A dermoscopic photograph of a skin lesion.
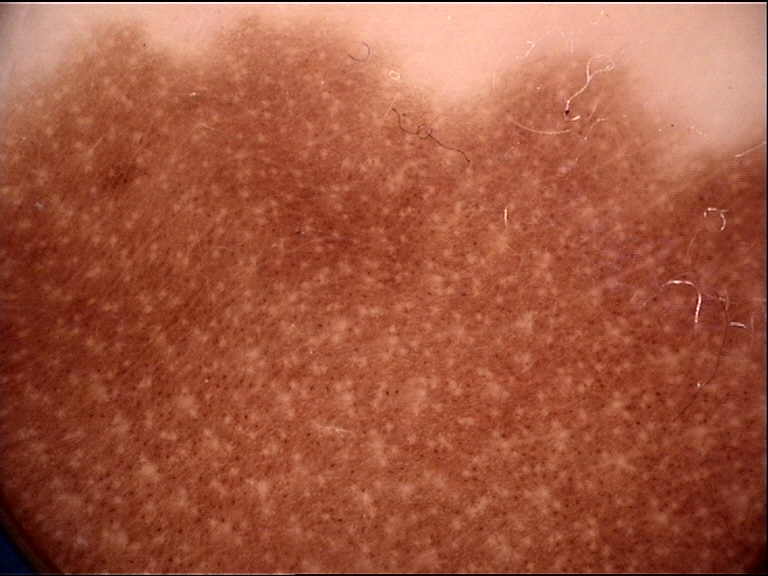lesion_type:
  main_class: banal
  pattern: compound
diagnosis:
  name: congenital compound nevus
  code: ccb
  malignancy: benign
  super_class: melanocytic
  confirmation: expert consensus